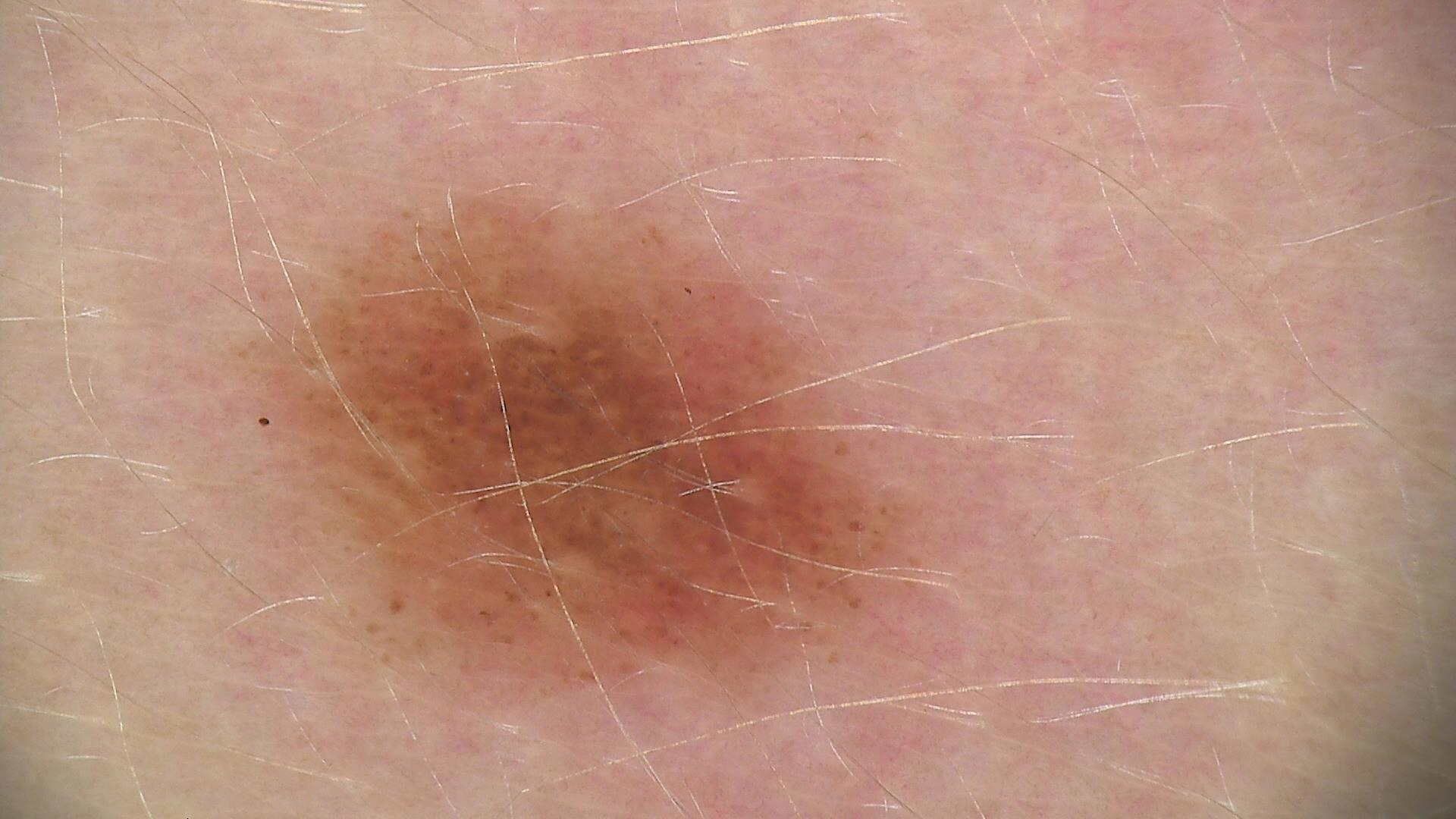image: dermoscopy
diagnosis:
  name: dysplastic junctional nevus
  code: jd
  malignancy: benign
  super_class: melanocytic
  confirmation: expert consensus